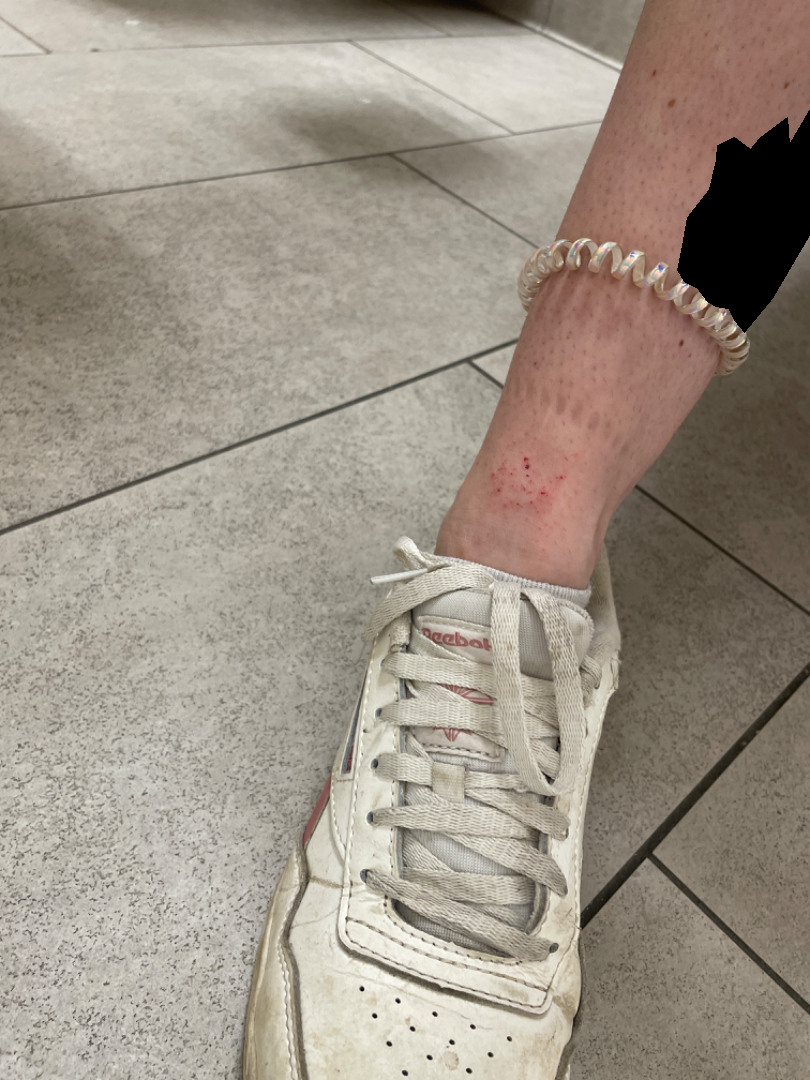{
  "patient_category": "a rash",
  "symptoms": [
    "burning",
    "enlargement",
    "itching"
  ],
  "body_site": [
    "top or side of the foot",
    "leg",
    "back of the hand"
  ],
  "shot_type": "at a distance",
  "differential": {
    "leading": [
      "Superficial wound of body region"
    ],
    "considered": [
      "Inflicted skin lesions"
    ],
    "unlikely": [
      "Irritant Contact Dermatitis"
    ]
  }
}